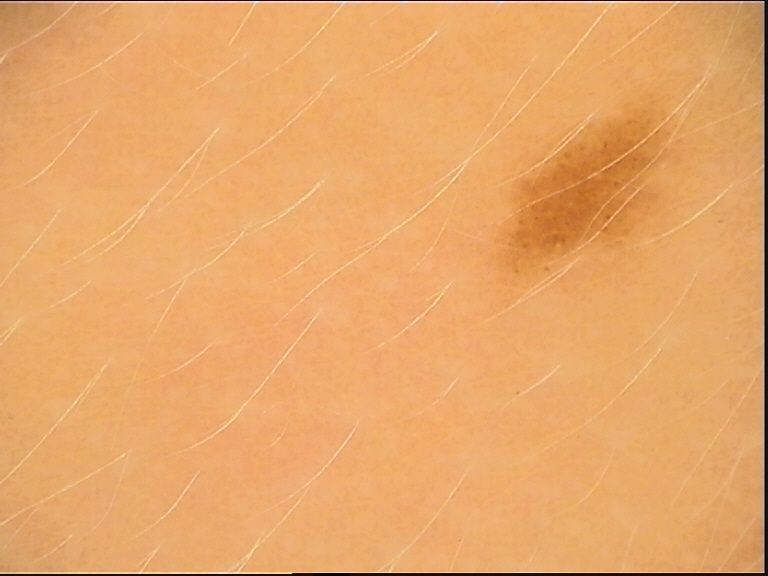imaging — dermatoscopy
diagnosis — dysplastic junctional nevus (expert consensus)